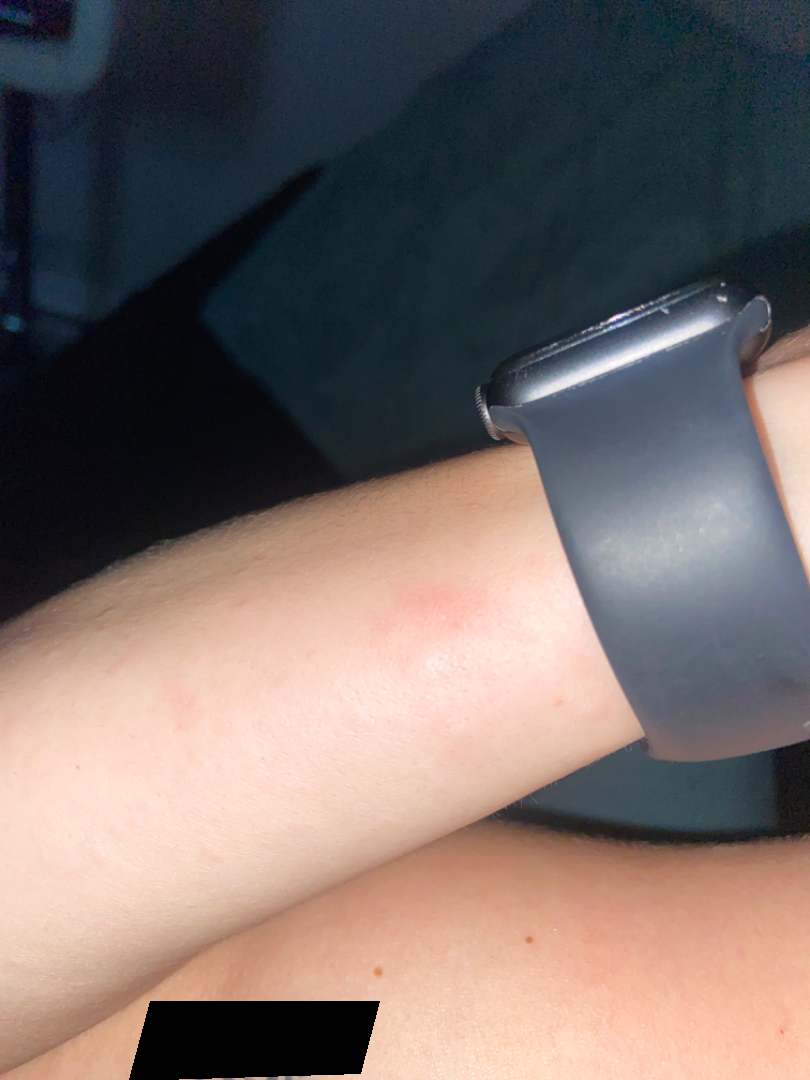Background: The lesion involves the arm. Close-up view. Findings: On dermatologist assessment of the image: the primary impression is Acne urticata; also consider Eczema.